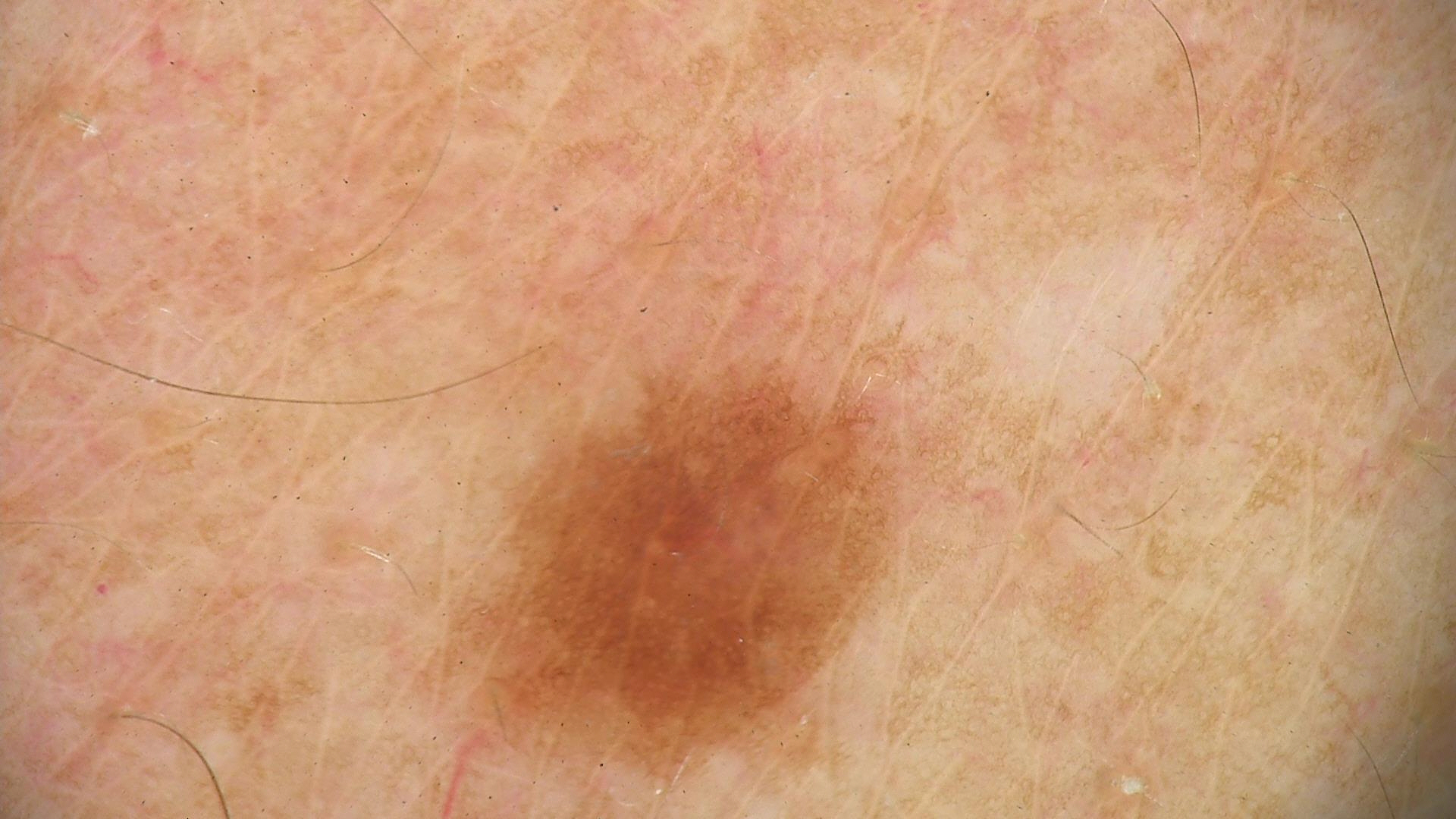A dermatoscopic image of a skin lesion. Diagnosed as a dysplastic junctional nevus.